This is a dermoscopic photograph of a skin lesion — 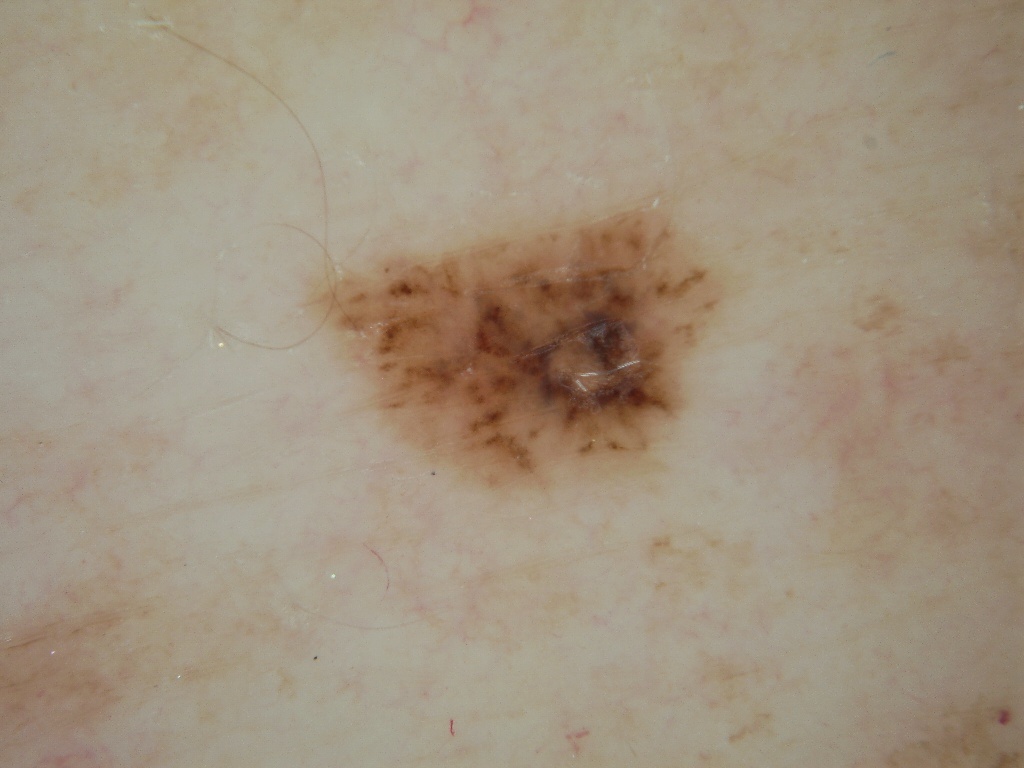Image and clinical context: With coordinates (x1, y1, x2, y2), the lesion is bounded by <bbox>311, 190, 725, 493</bbox>. Dermoscopically, the lesion shows no pigment network, globules, negative network, milia-like cysts, or streaks. Conclusion: Histopathology confirmed a melanoma.